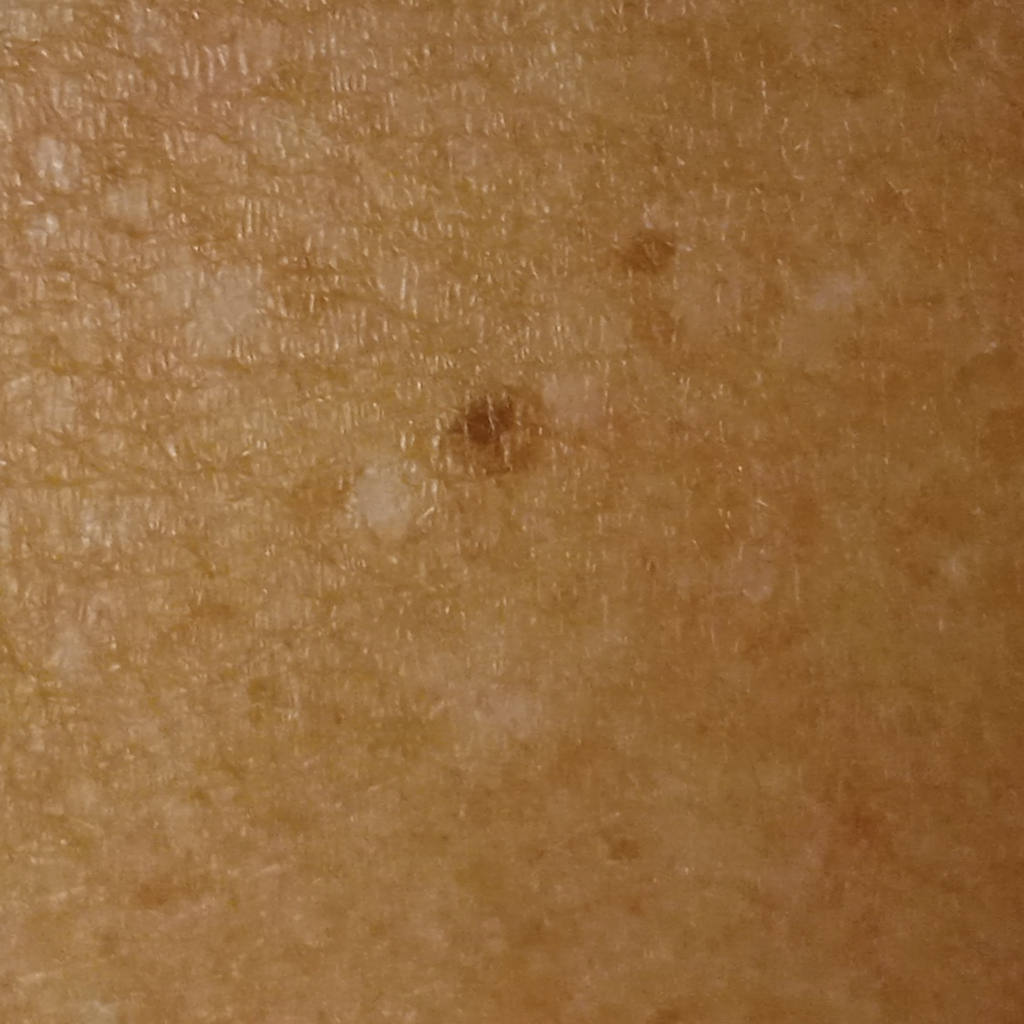The patient reports a personal history of skin cancer and a personal history of cancer.
Acquired for a research image collection, with no referral diagnosis.
The patient says their skin tans without first burning.
The patient describes having a moderate number of moles.
A clinical close-up of a skin lesion.
A female subject 75 years of age.
Measuring roughly 2.7 mm.
The dermatologists' assessment was a melanocytic nevus.